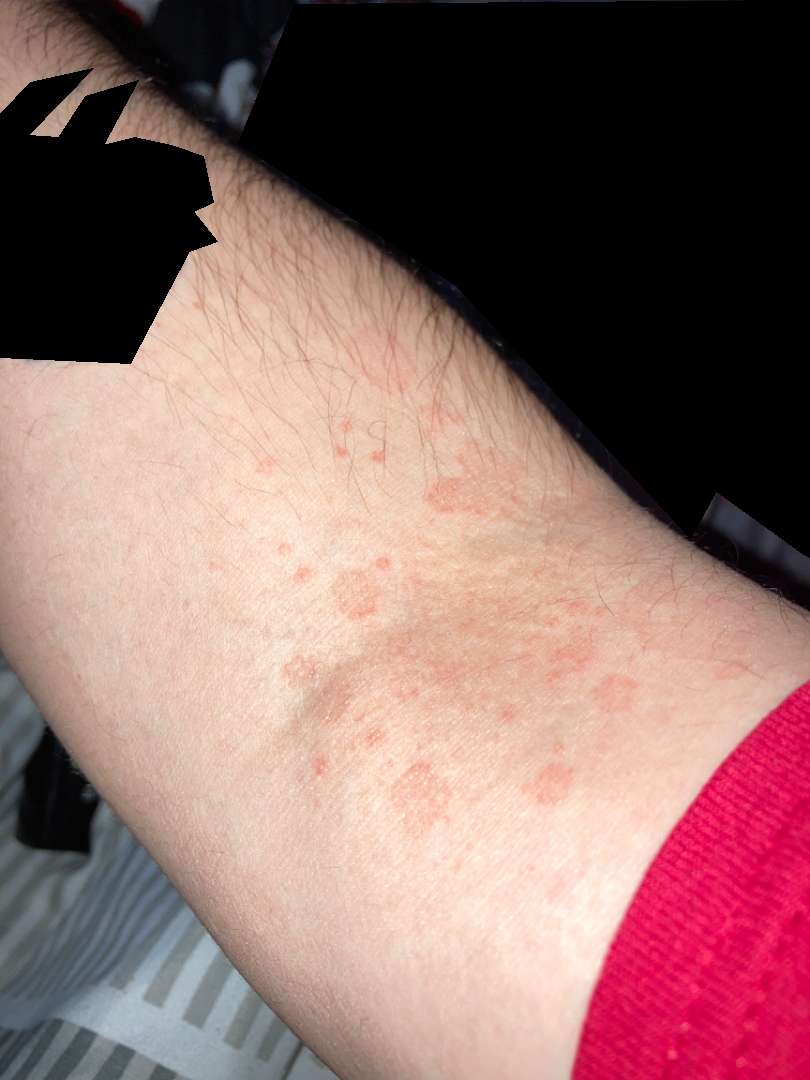anatomic site = arm
photo taken = at an angle
patient = male, age 18–29
assessment = the differential includes Drug Rash, Viral Exanthem and Eczema, with no clear leading consideration